A dermatoscopic image of a skin lesion: 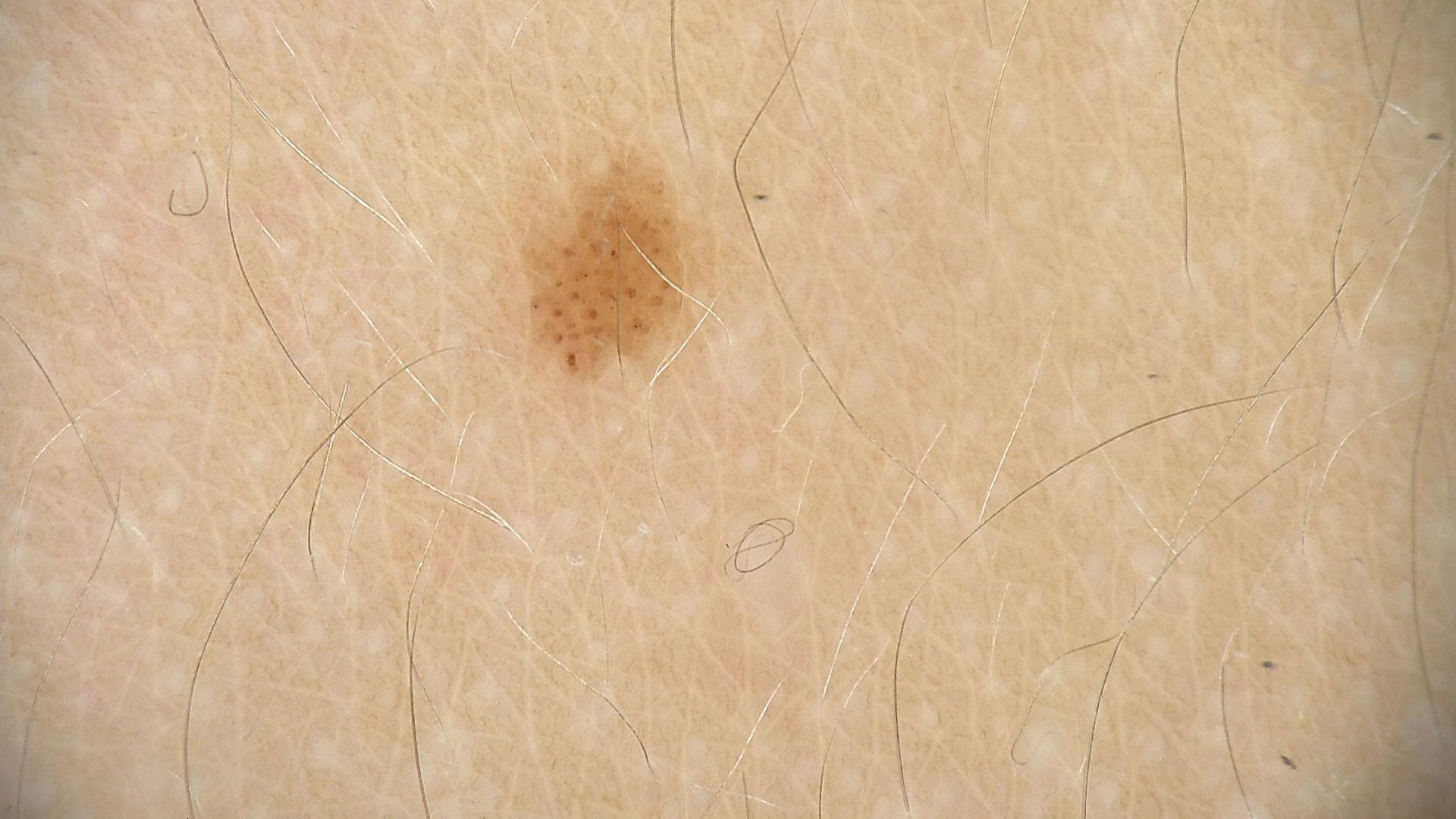Findings:
• assessment: dysplastic junctional nevus (expert consensus)